The patient says their skin reddens with sun exposure. Few moles overall by the patient's own estimate. Imaged for a research study, with no referral diagnosis recorded. A clinical photograph of a skin lesion. A male patient 72 years of age. On a questionnaire the patient reported a personal history of cancer — 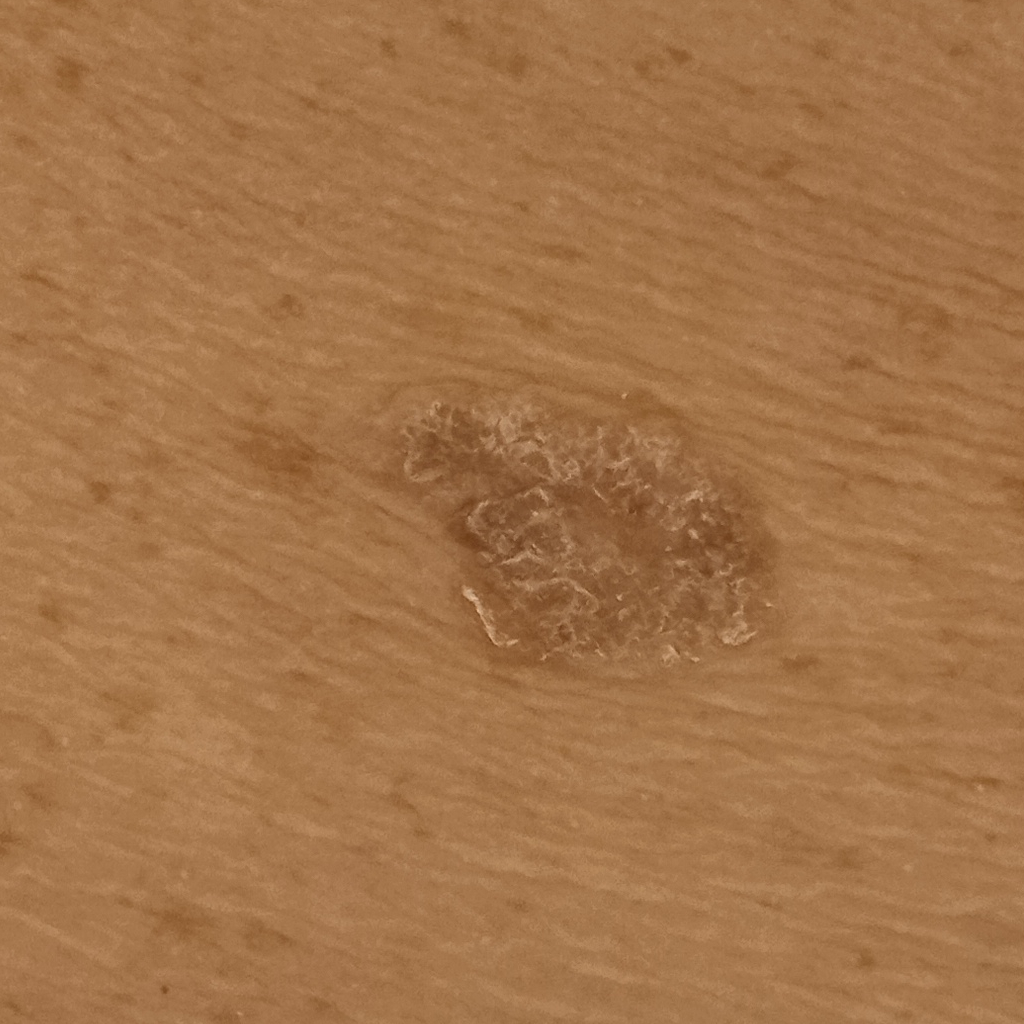| field | value |
|---|---|
| location | the back |
| size | 16.5 mm |
| diagnosis | seborrheic keratosis (dermatologist consensus) |